A dermoscopic image of a skin lesion:
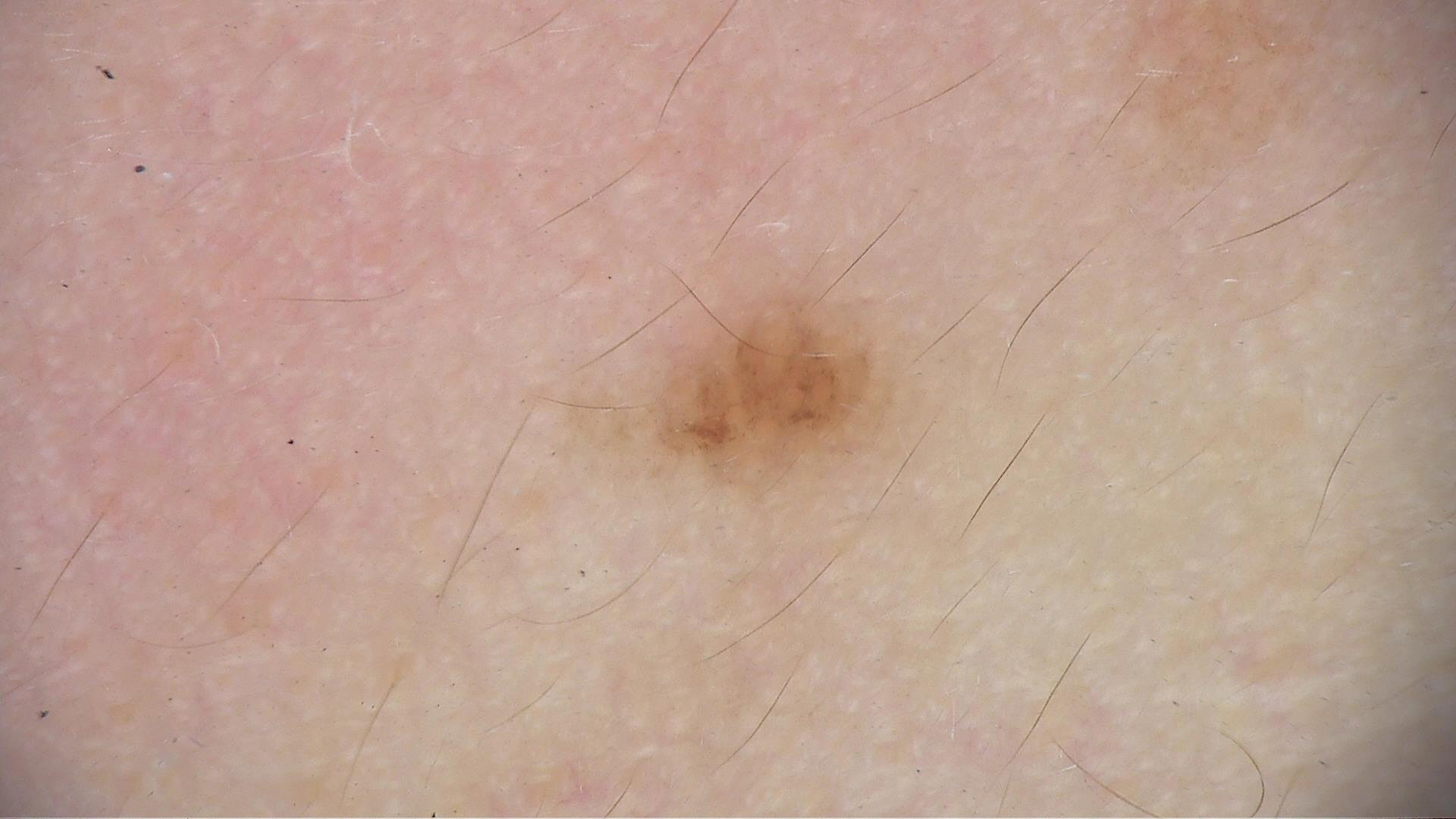Q: What is the diagnosis?
A: Miescher nevus (expert consensus)